A close-up photograph; located on the back of the hand and palm; male patient, age 18–29 — 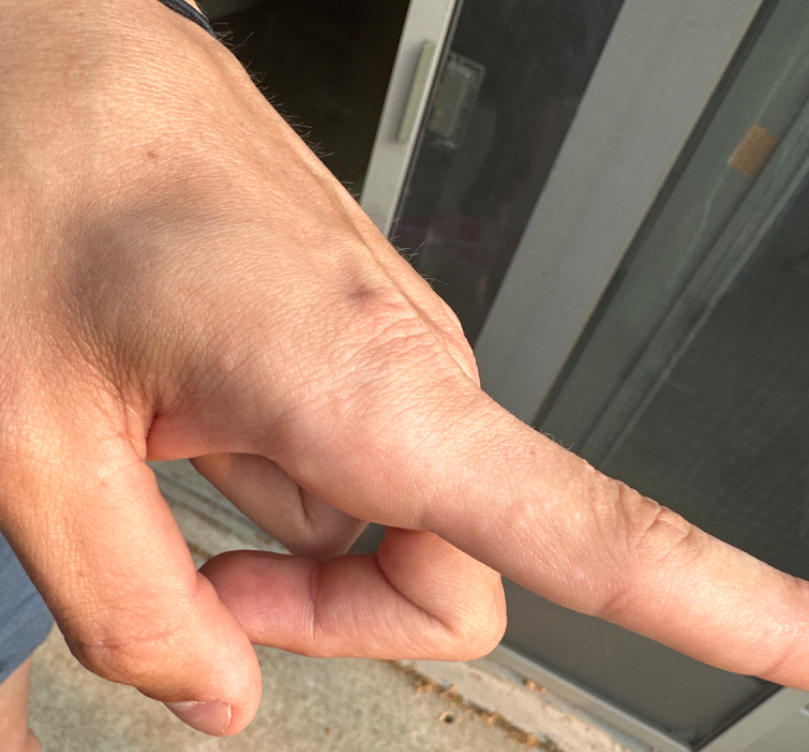The reviewer was unable to grade this case for skin condition.